A dermoscopy image of a single skin lesion: 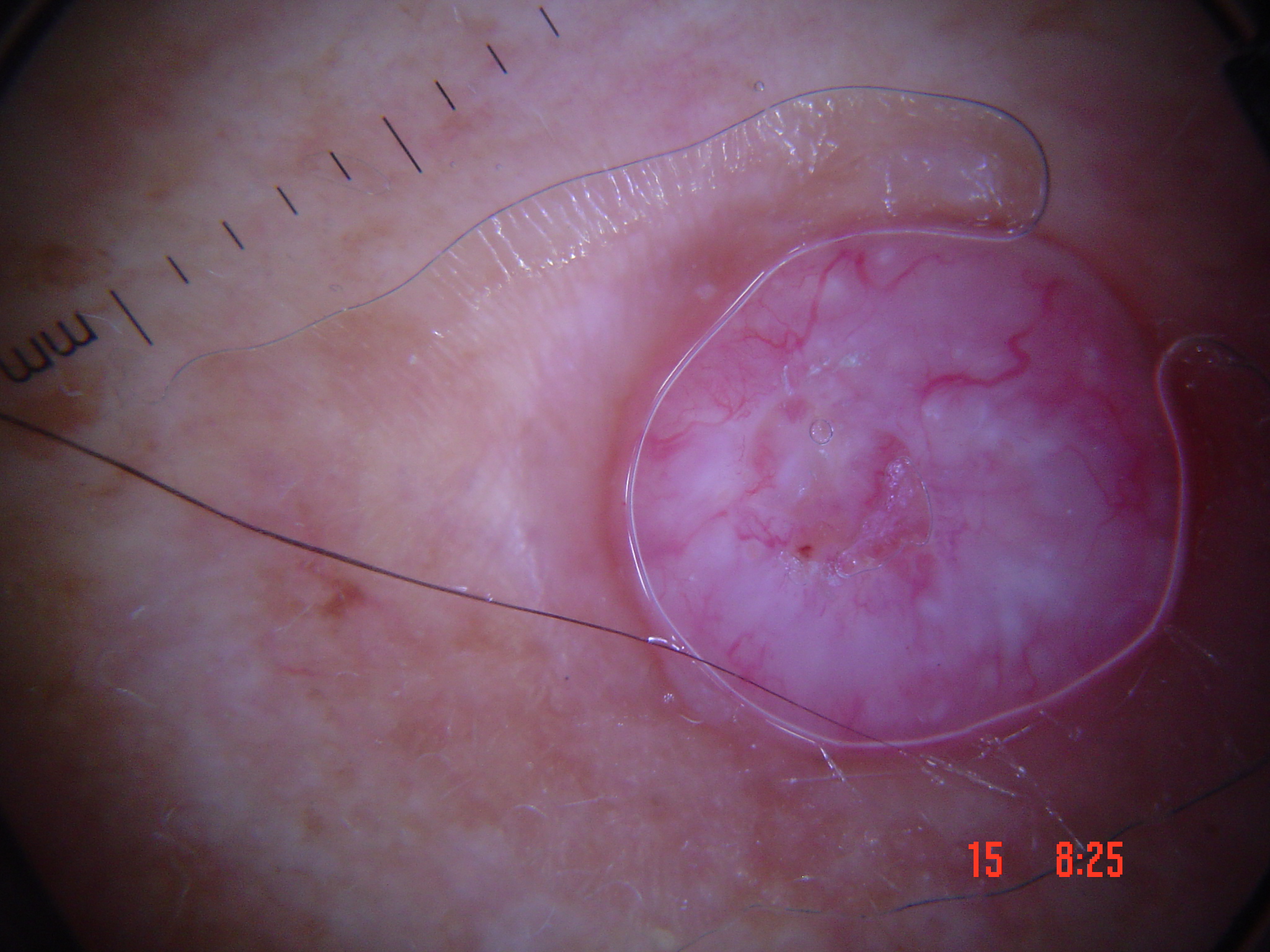category: keratinocytic
diagnostic label: squamous cell carcinoma (biopsy-proven)